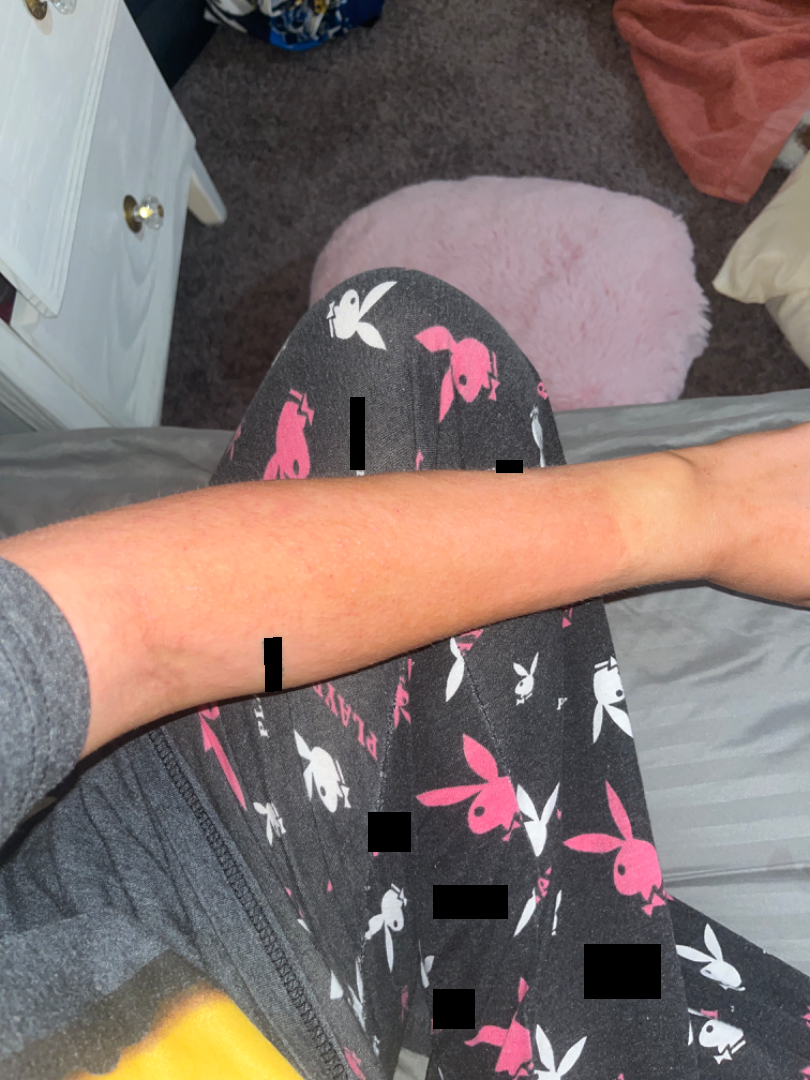assessment: could not be assessed; location: arm, leg, back of the torso and front of the torso; image framing: at a distance.